A dermoscopic photograph of a skin lesion:
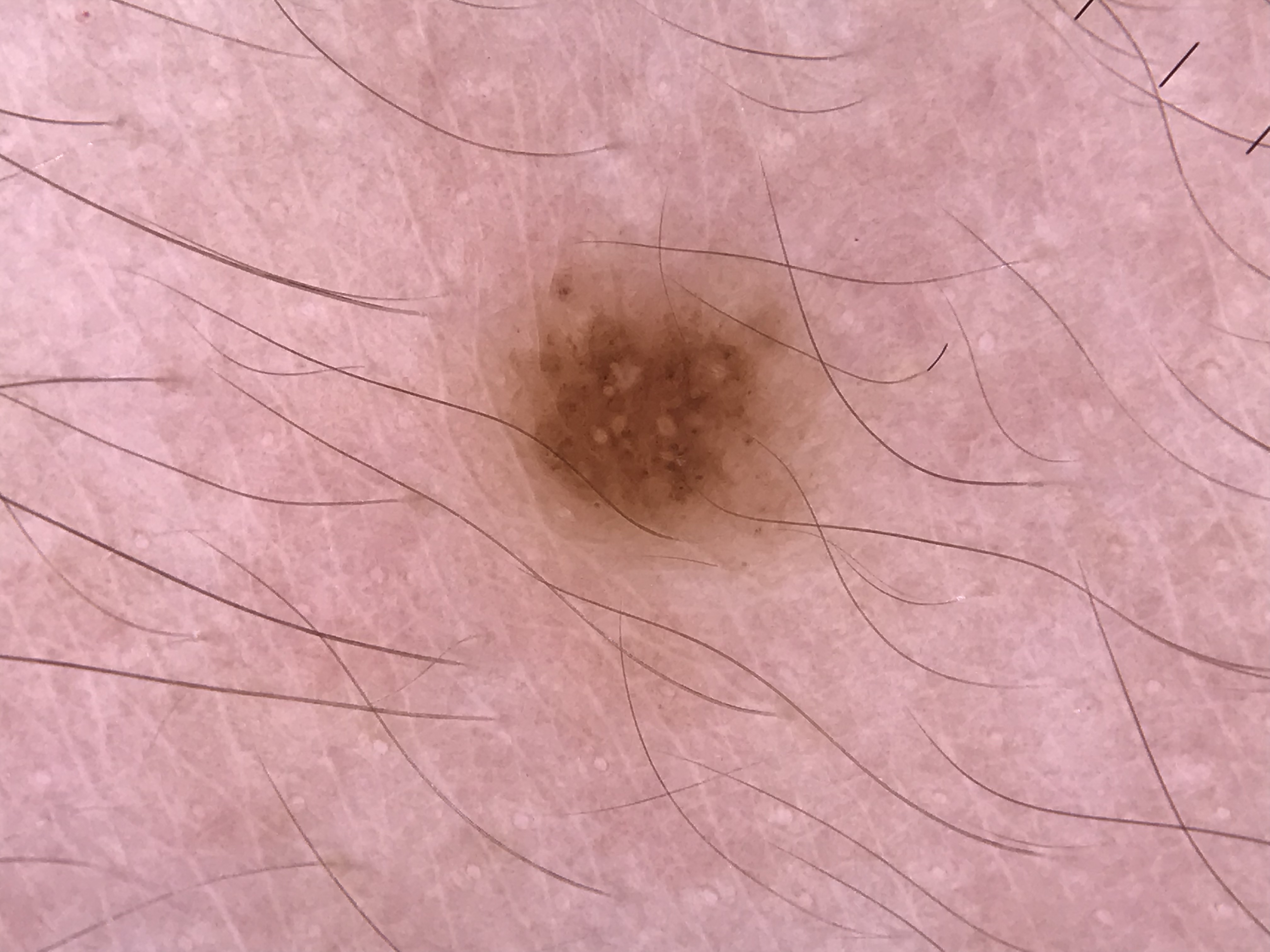Labeled as a dysplastic compound nevus.